The patient reported no systemic symptoms; the affected area is the palm; a close-up photograph; human graders estimated MST 2–3; reported duration is about one day; texture is reported as raised or bumpy; the lesion is associated with itching: 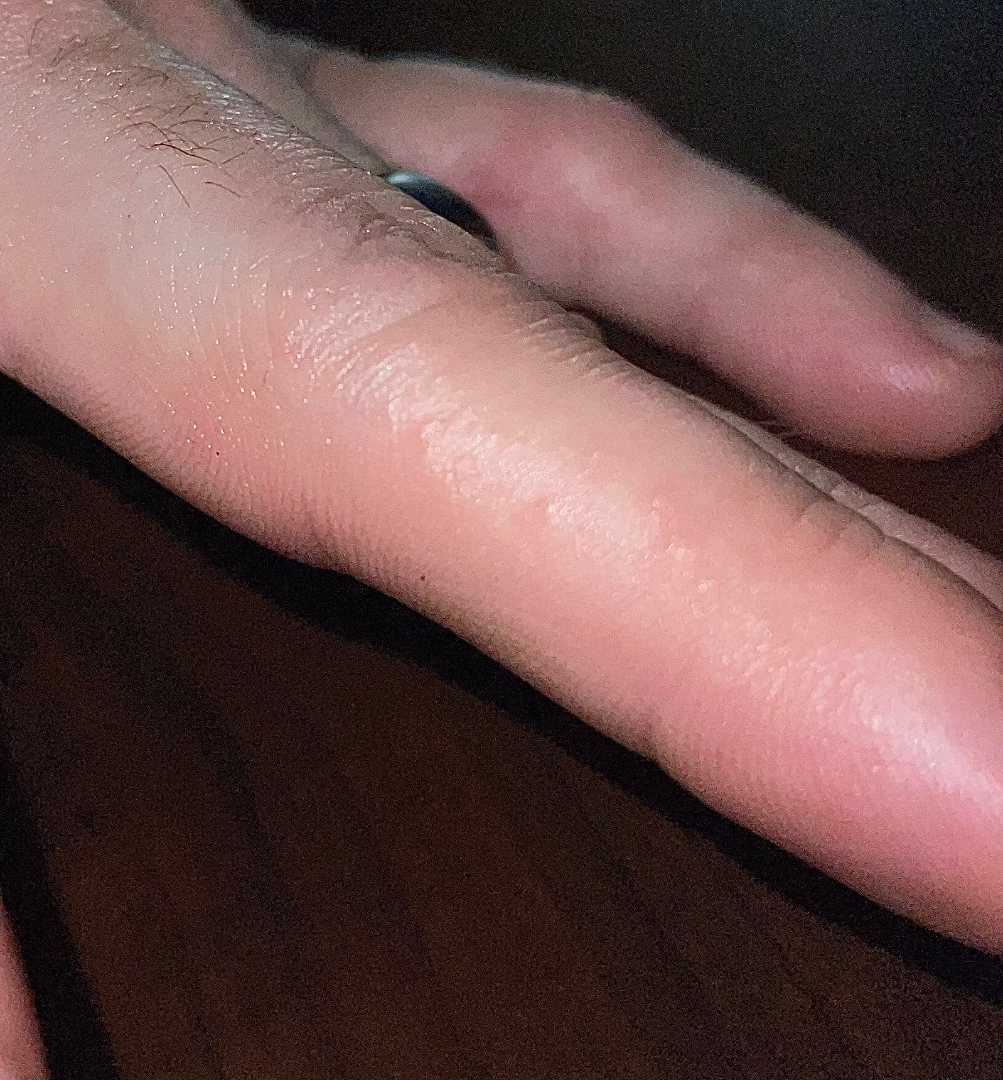{
  "differential": {
    "leading": [
      "Hypersensitivity"
    ]
  }
}